A skin lesion imaged with a dermatoscope: 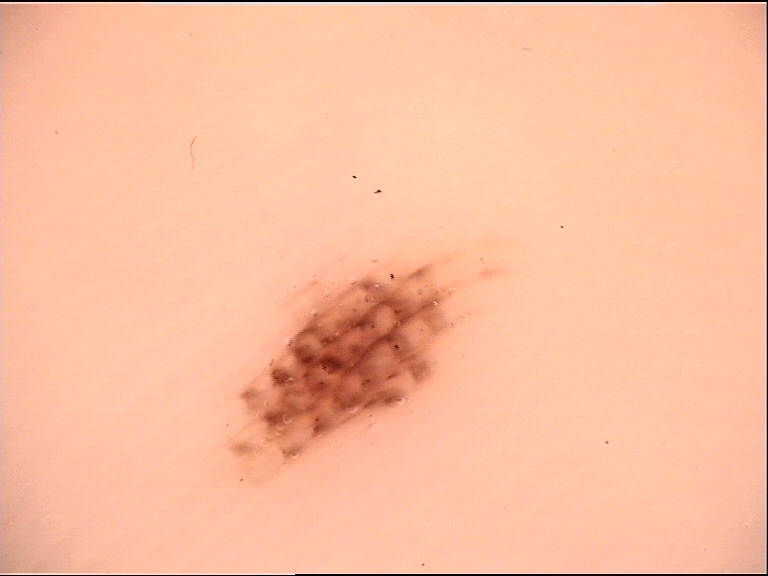<case>
  <lesion_type>
    <main_class>banal</main_class>
    <pattern>junctional</pattern>
  </lesion_type>
  <diagnosis>
    <name>acral junctional nevus</name>
    <code>ajb</code>
    <malignancy>benign</malignancy>
    <super_class>melanocytic</super_class>
    <confirmation>expert consensus</confirmation>
  </diagnosis>
</case>